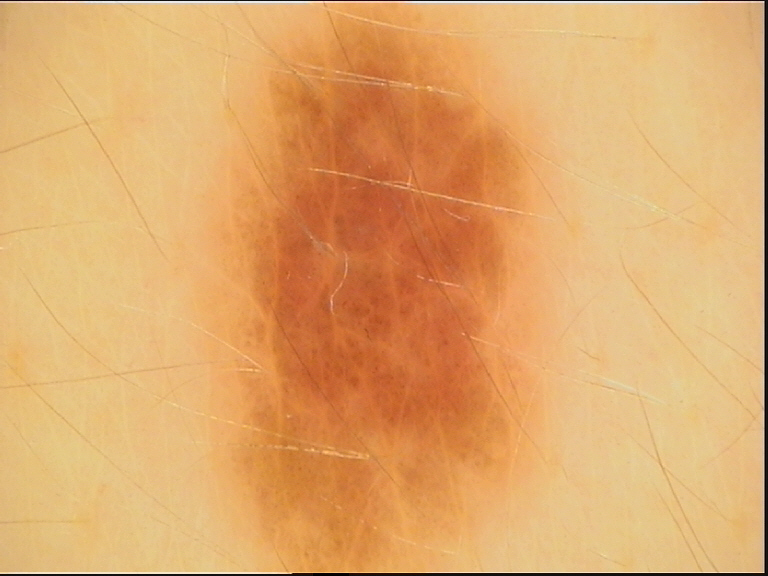Labeled as a dysplastic junctional nevus.